A clinical photograph of a skin lesion; a subject 45 years old — 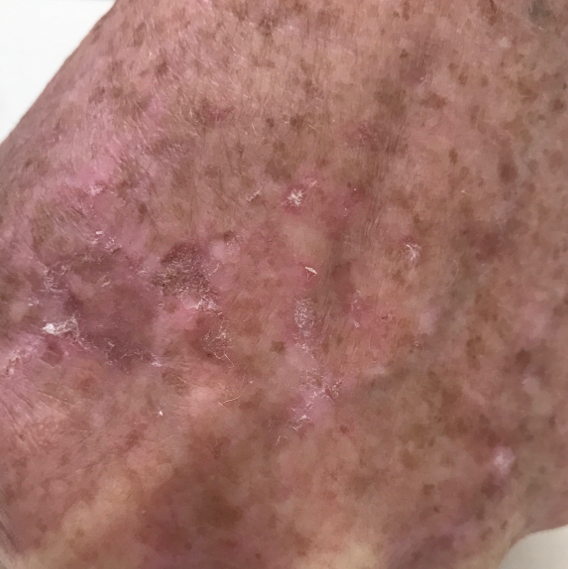Q: What is the anatomic site?
A: a hand
Q: What is the diagnosis?
A: actinic keratosis (clinical consensus)